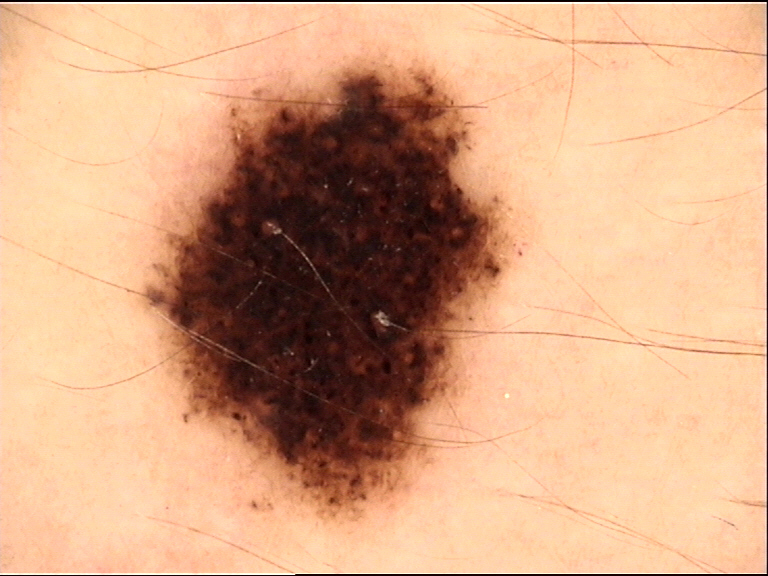Case:
A dermoscopic image of a skin lesion.
Impression:
Consistent with a dysplastic compound nevus.